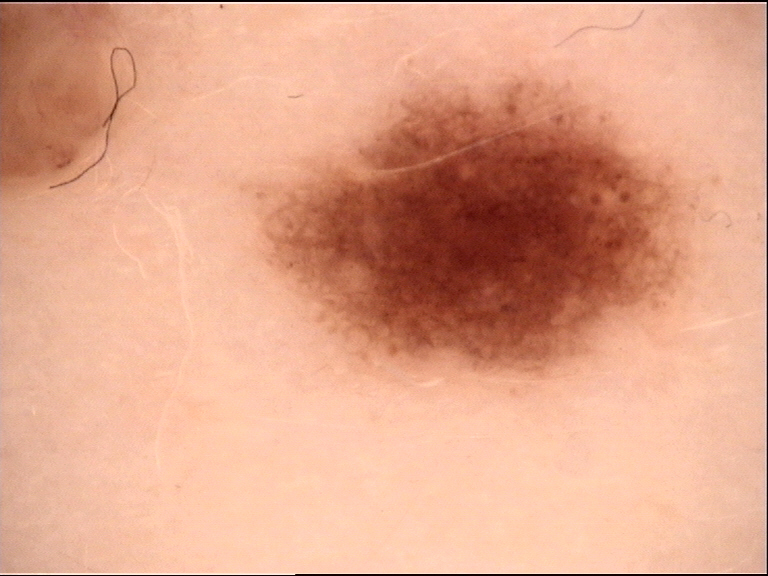  image: dermatoscopy
  diagnosis:
    name: dysplastic junctional nevus
    code: jd
    malignancy: benign
    super_class: melanocytic
    confirmation: expert consensus